Acquired for a research image collection, with no referral diagnosis · a dermoscopic image of a skin lesion · a female patient 60 years old · the patient says their skin tans without first burning · few moles overall by the patient's own estimate: 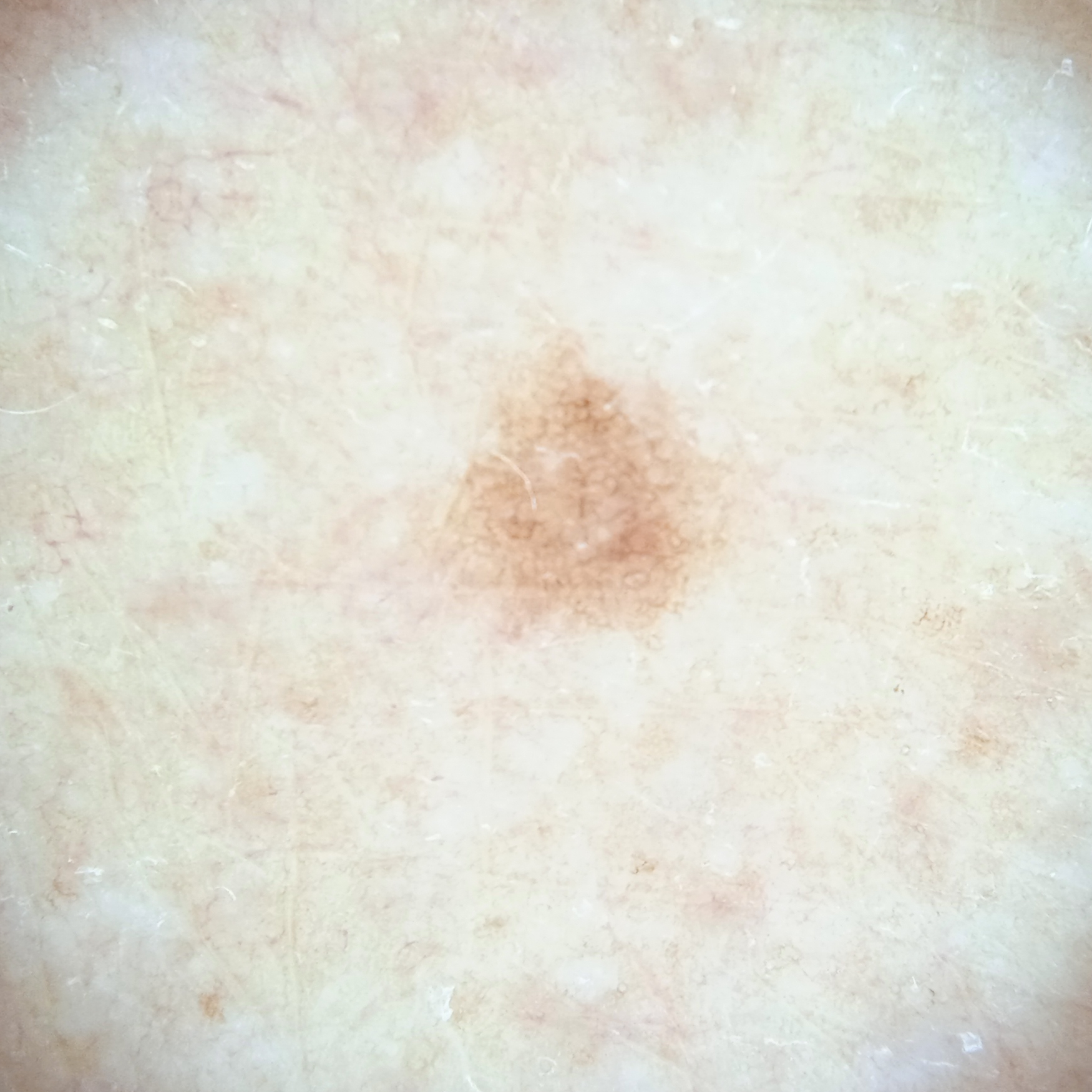site: an arm; lesion size: 2.8 mm; diagnostic label: melanocytic nevus (dermatologist consensus).